A dermatoscopic image of a skin lesion:
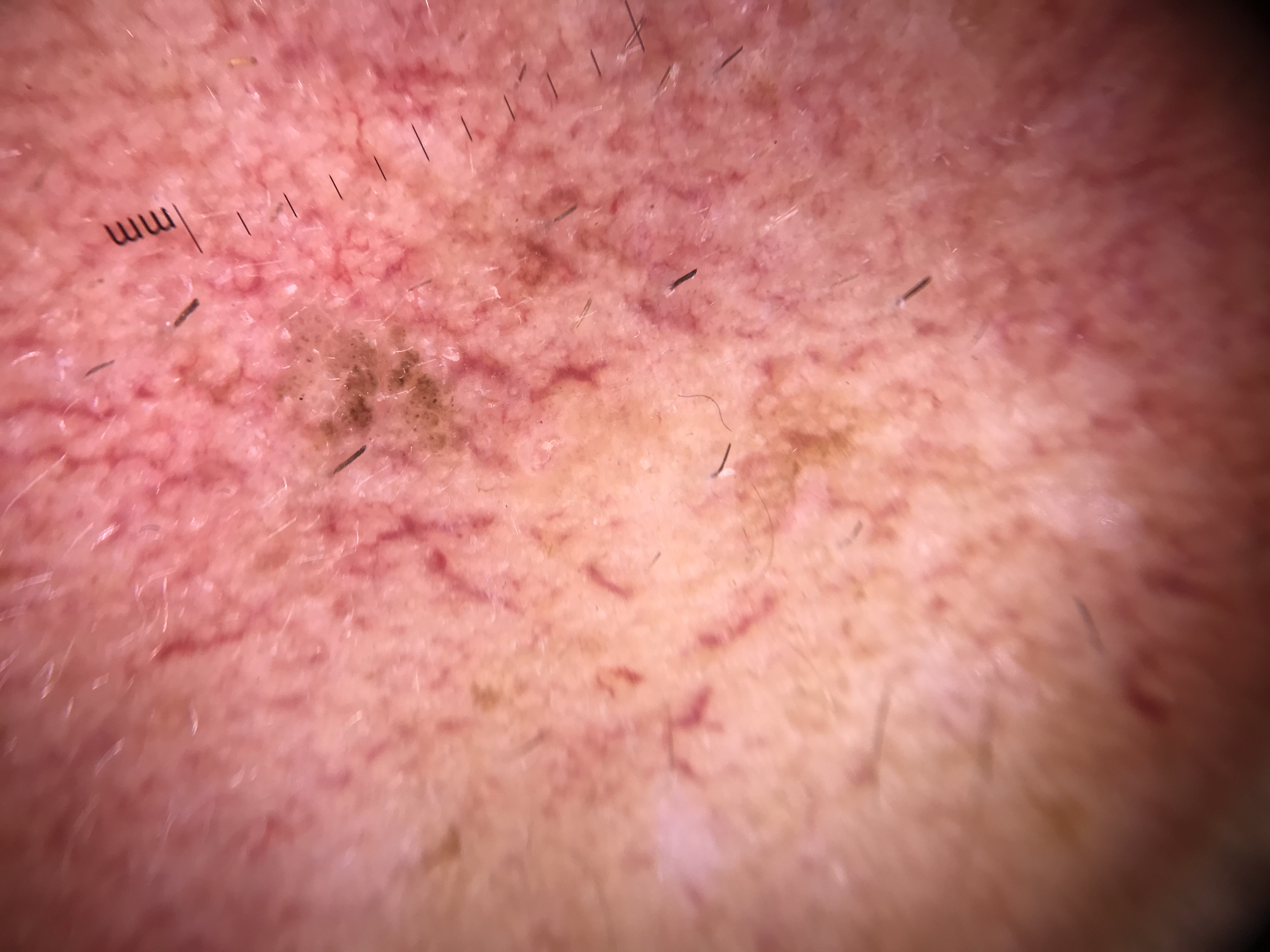Diagnosed as a seborrheic keratosis.